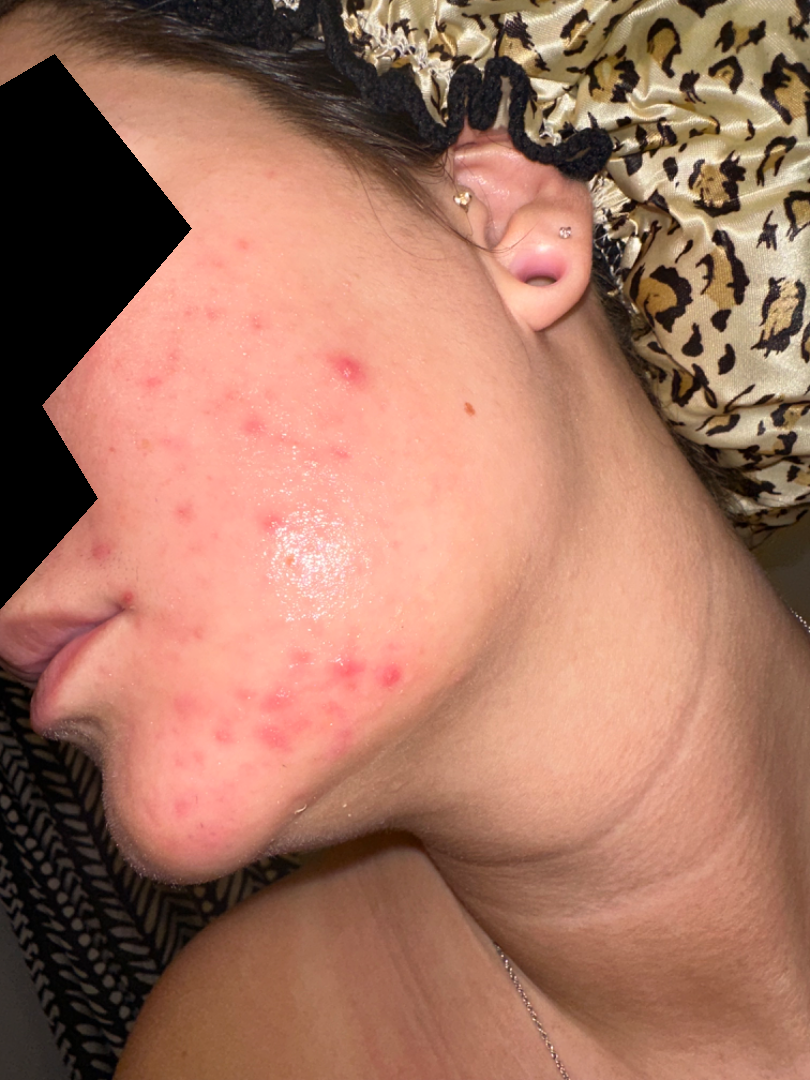Review: A single dermatologist reviewed the case: favoring Acne; possibly Rosacea; also raised was Perioral Dermatitis.